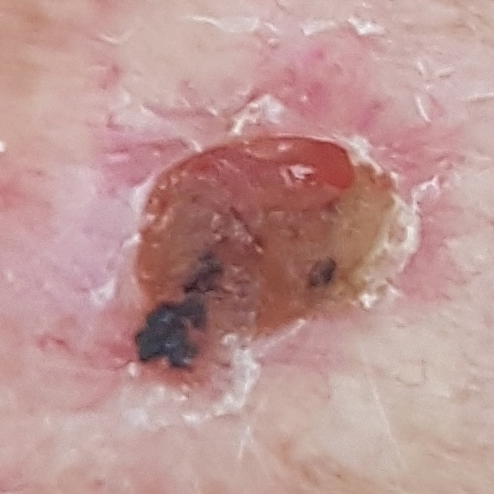diagnostic label: basal cell carcinoma (biopsy-proven).